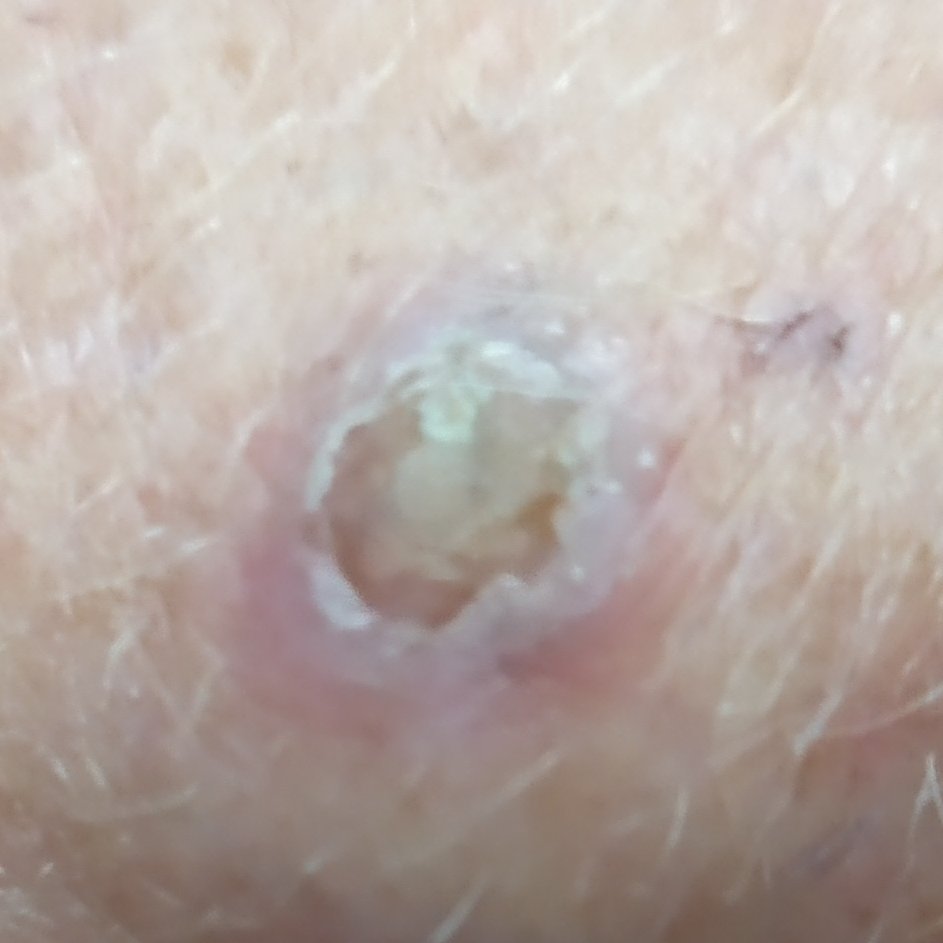A smartphone photograph of a skin lesion.
By history, prior malignancy (patient or family) and prior skin cancer (patient or family).
The lesion is located on a hand.
The lesion is roughly 11 by 10 mm.
Per patient report, the lesion itches and is elevated, but does not hurt and has not bled.
The biopsy diagnosis was a squamous cell carcinoma.